A clinical close-up of a skin lesion. A male subject aged 83:
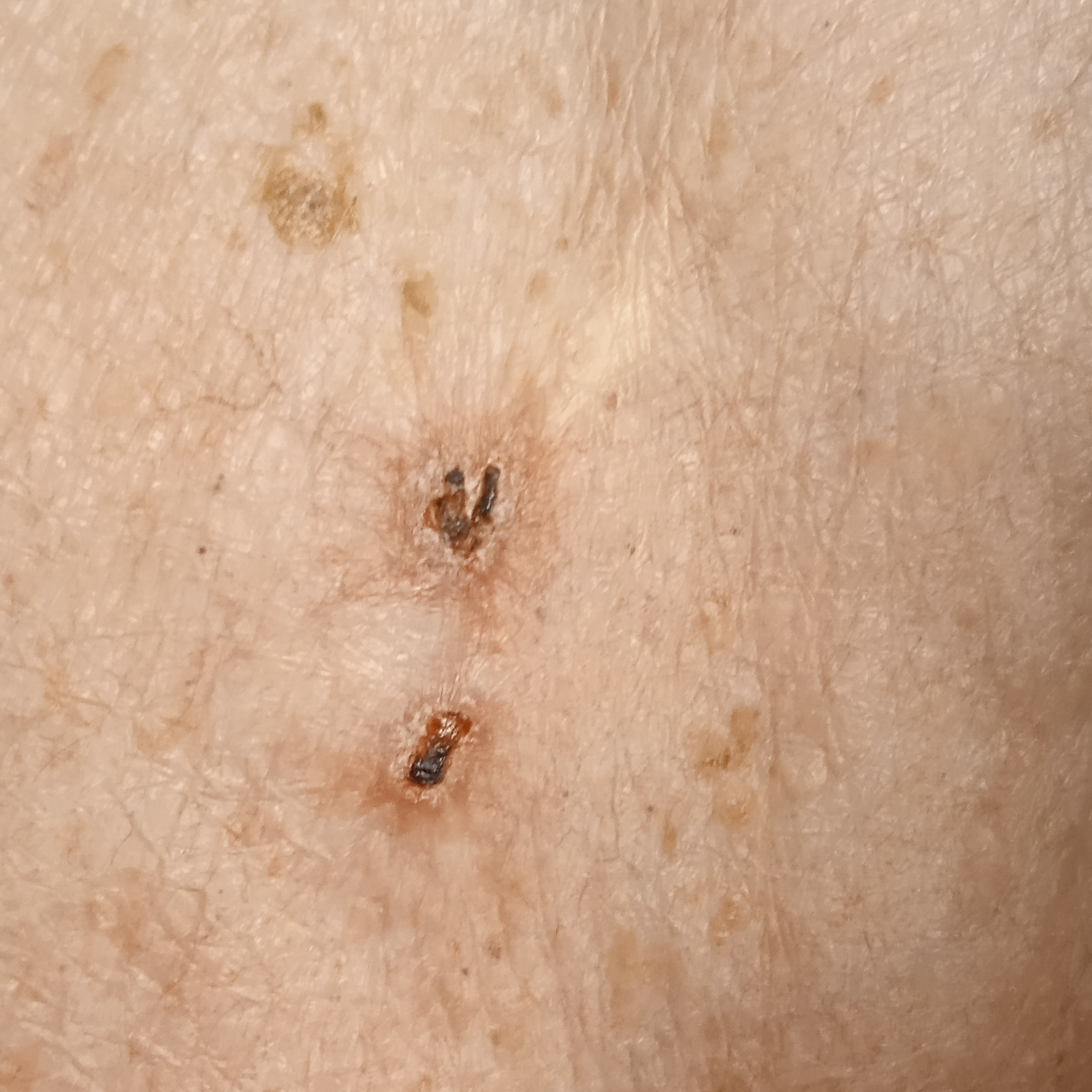Case summary:
The lesion is on the back.
Conclusion:
The diagnostic impression was a basal cell carcinoma.